Texture is reported as raised or bumpy. The arm is involved. The photograph is a close-up of the affected area:
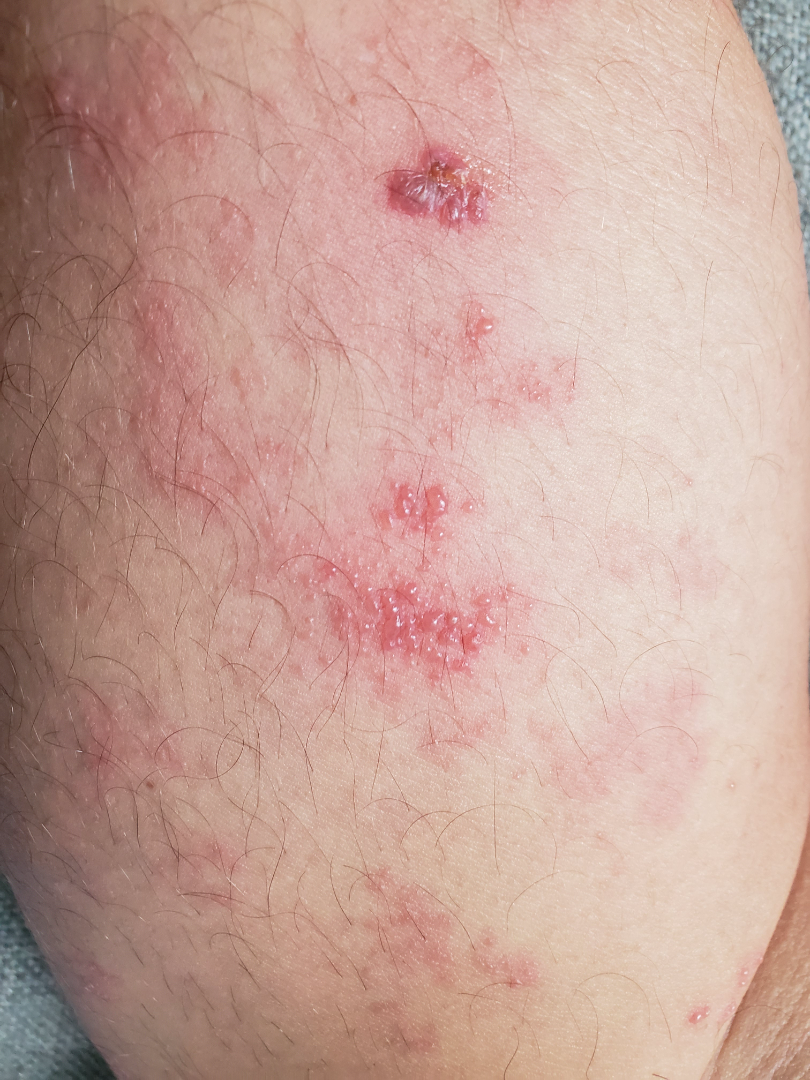assessment = not assessable.